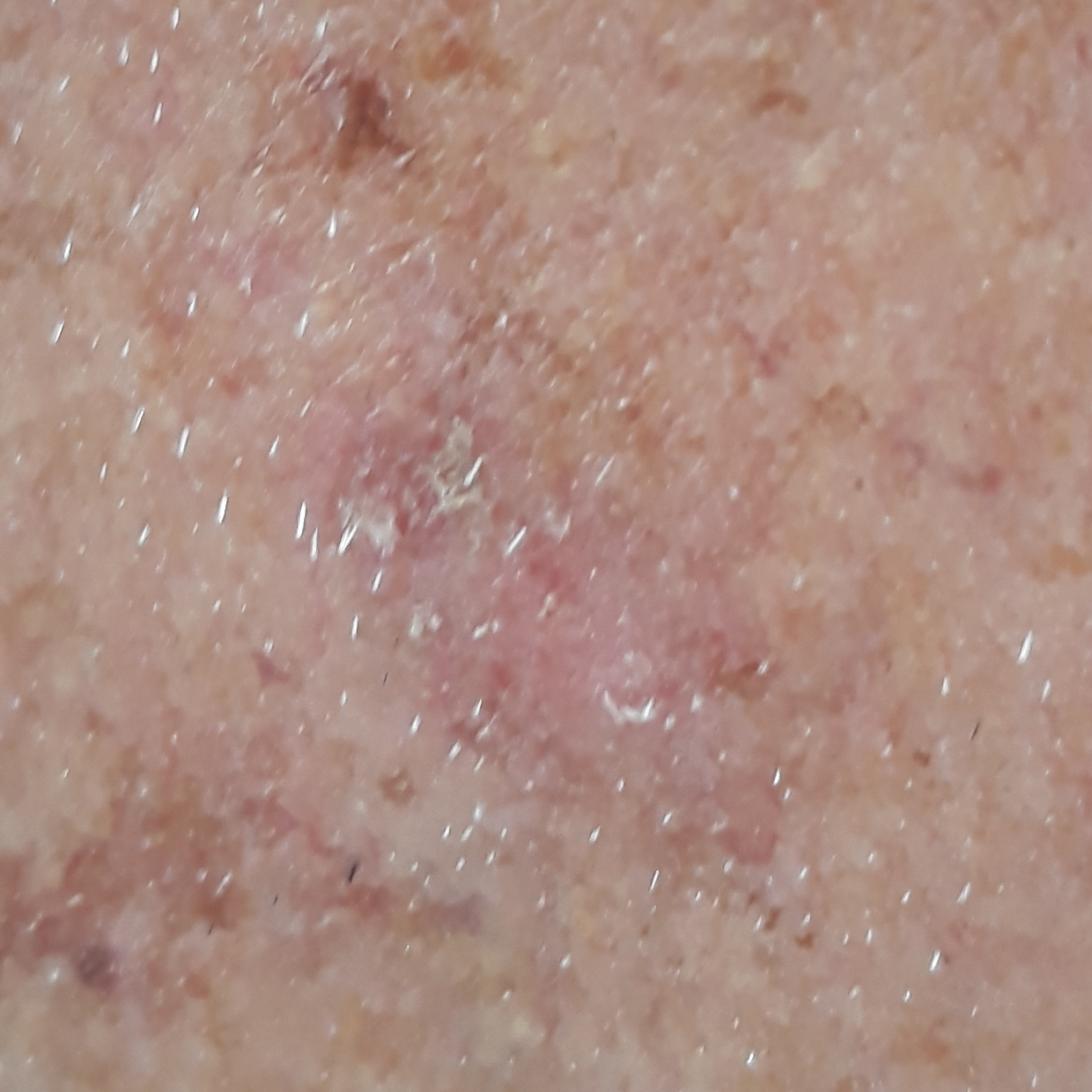Patient and lesion: A patient age 77. Impression: Expert review favored an actinic keratosis.